The photograph was taken at an angle — 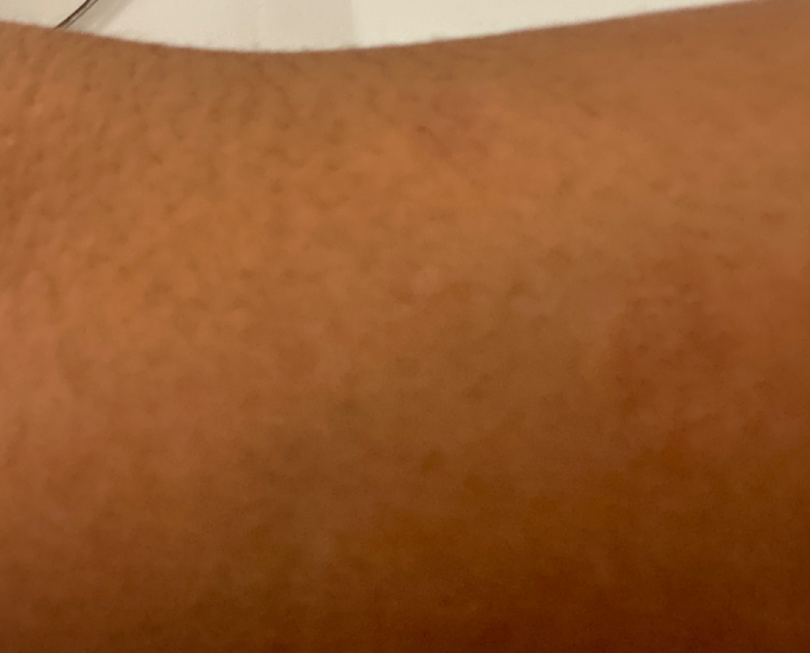No clear dermatological pathology was apparent in the photograph.